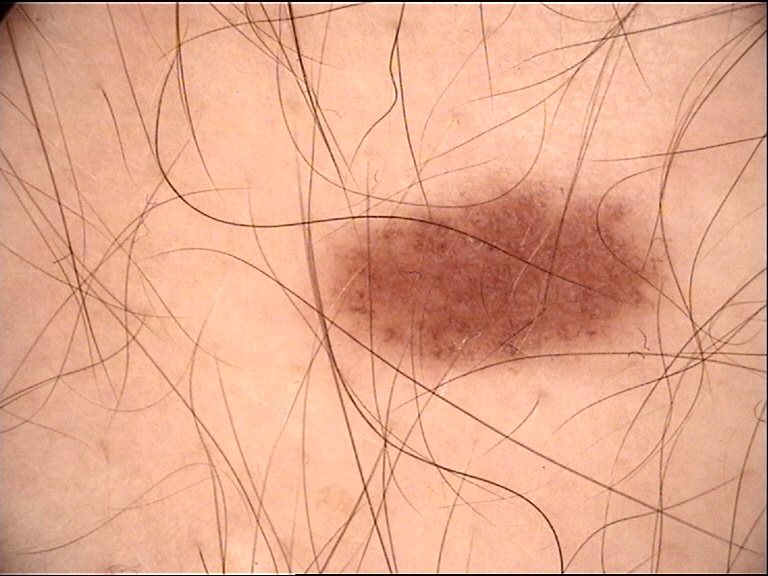The diagnosis was a dysplastic junctional nevus.